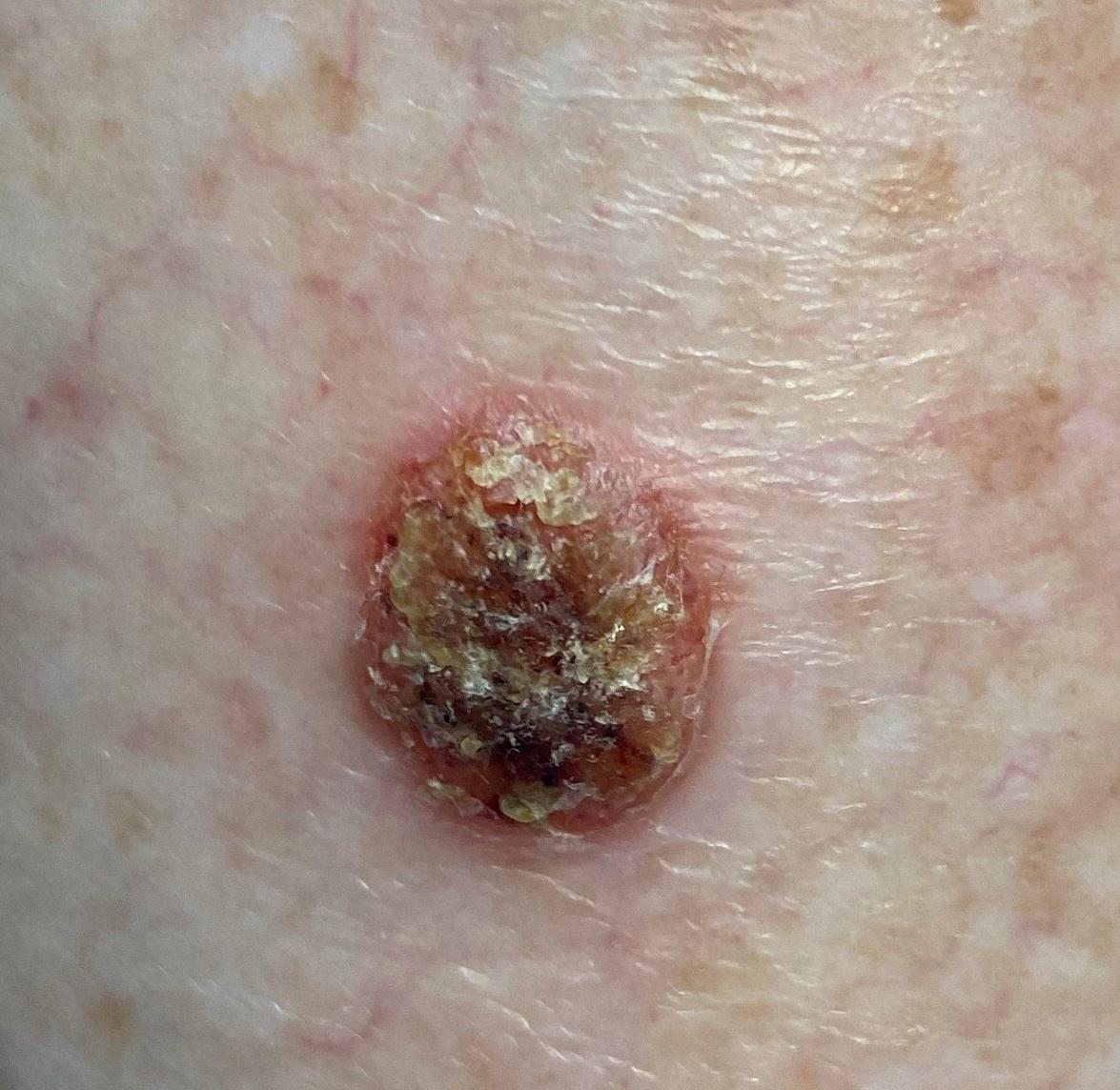subject=female, about 60 years old | FST=II | relevant background=no prior melanoma and no melanoma in first-degree relatives | imaging=clinical overview photograph | body site=a lower extremity | diagnostic label=Seborrheic keratosis (biopsy-proven).